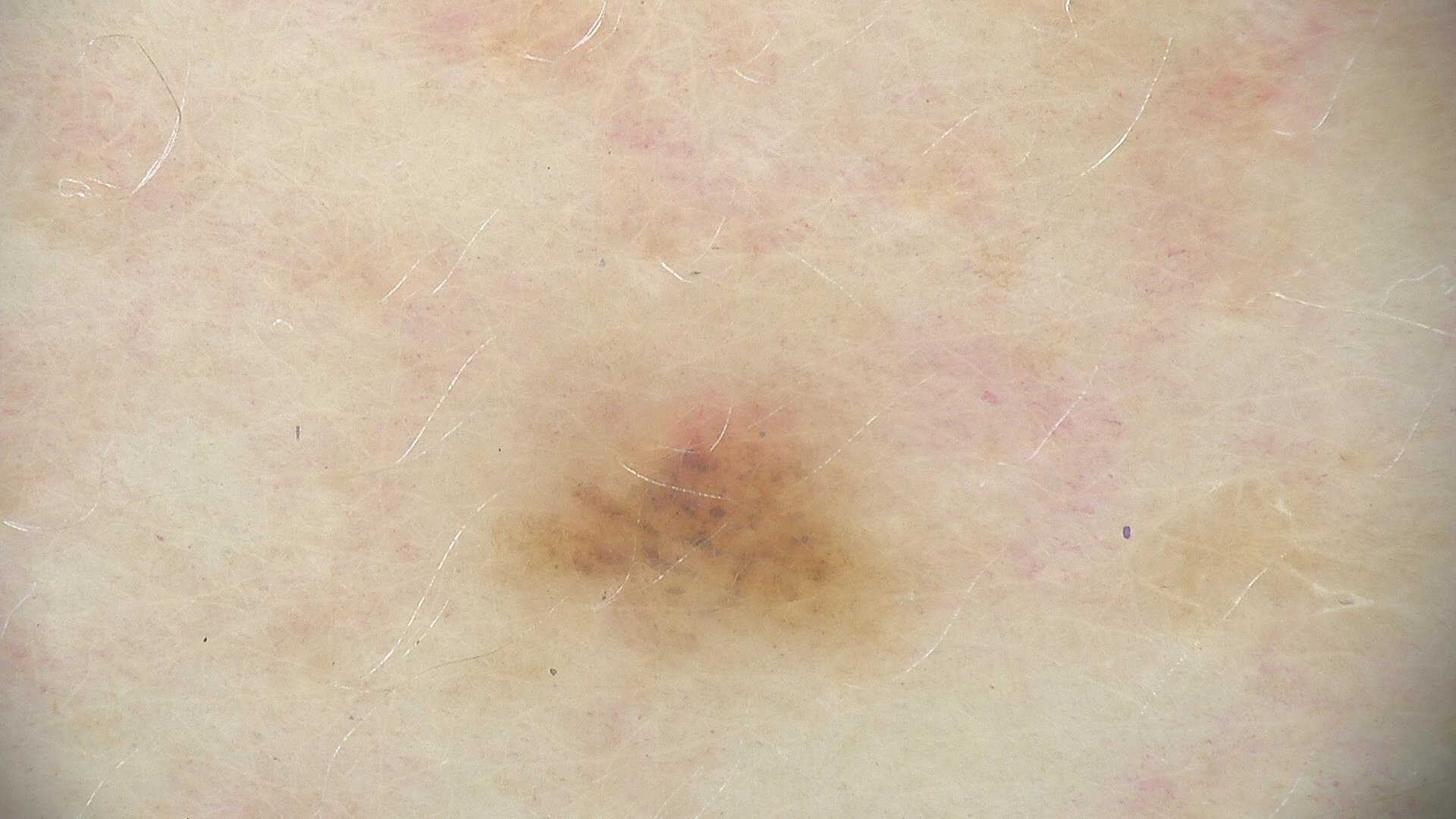{
  "image": "dermatoscopy",
  "diagnosis": {
    "name": "dysplastic junctional nevus",
    "code": "jd",
    "malignancy": "benign",
    "super_class": "melanocytic",
    "confirmation": "expert consensus"
  }
}